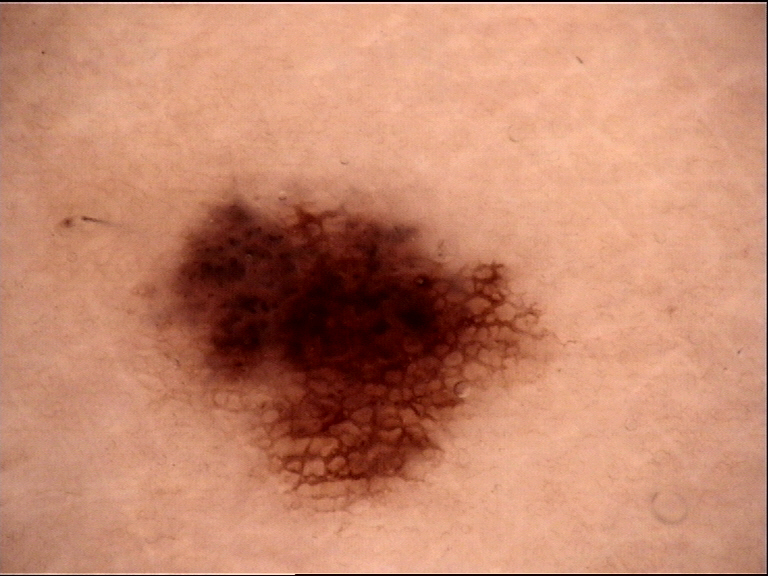A dermoscopic close-up of a skin lesion.
The diagnostic label was a benign lesion — a dysplastic junctional nevus.